Dermoscopy of a skin lesion.
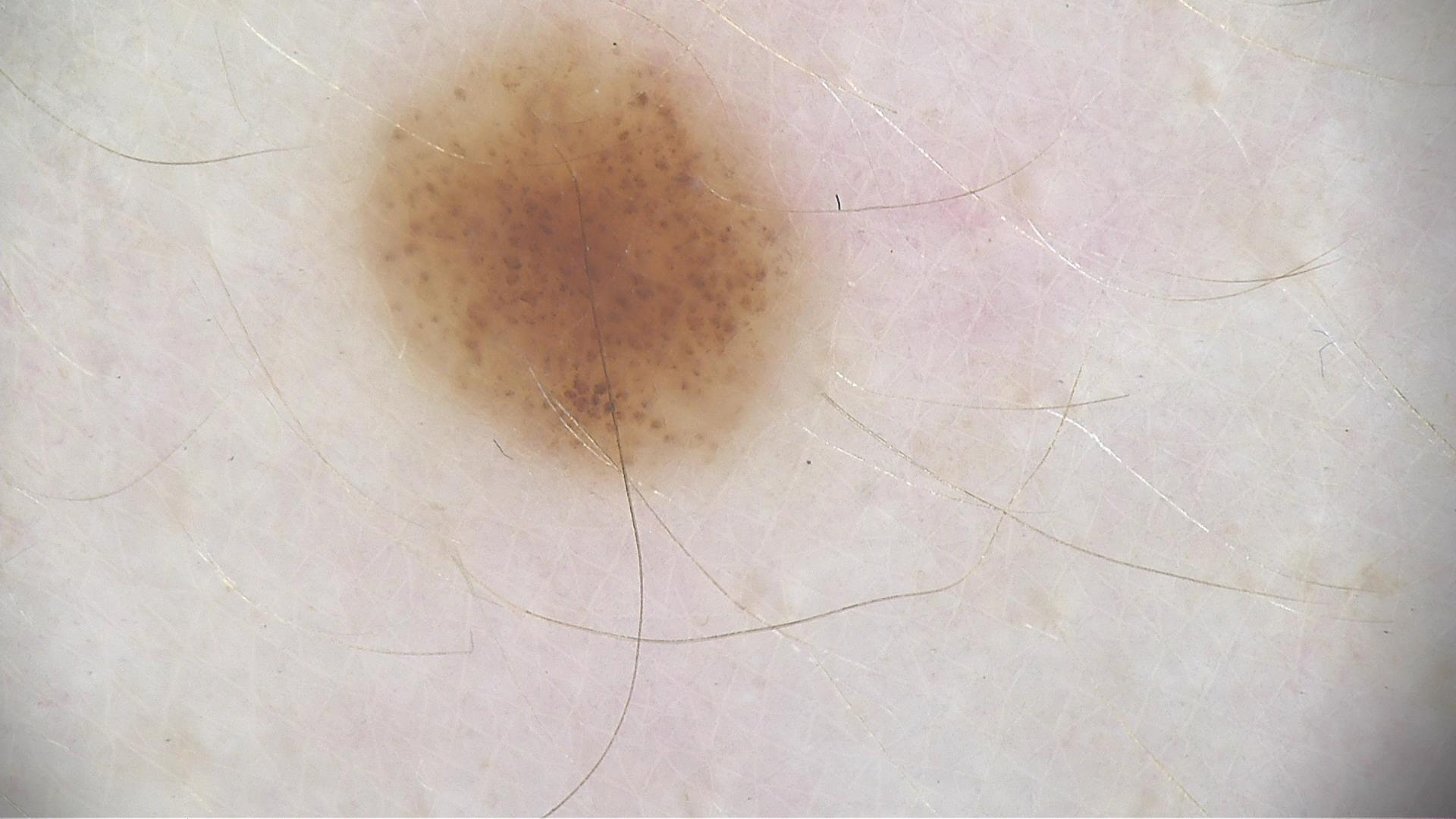The morphology is that of a banal lesion.
Labeled as a compound nevus.